The contributor is male, the lesion involves the leg, the photograph is a close-up of the affected area, texture is reported as raised or bumpy and rough or flaky, symptoms reported: itching and burning:
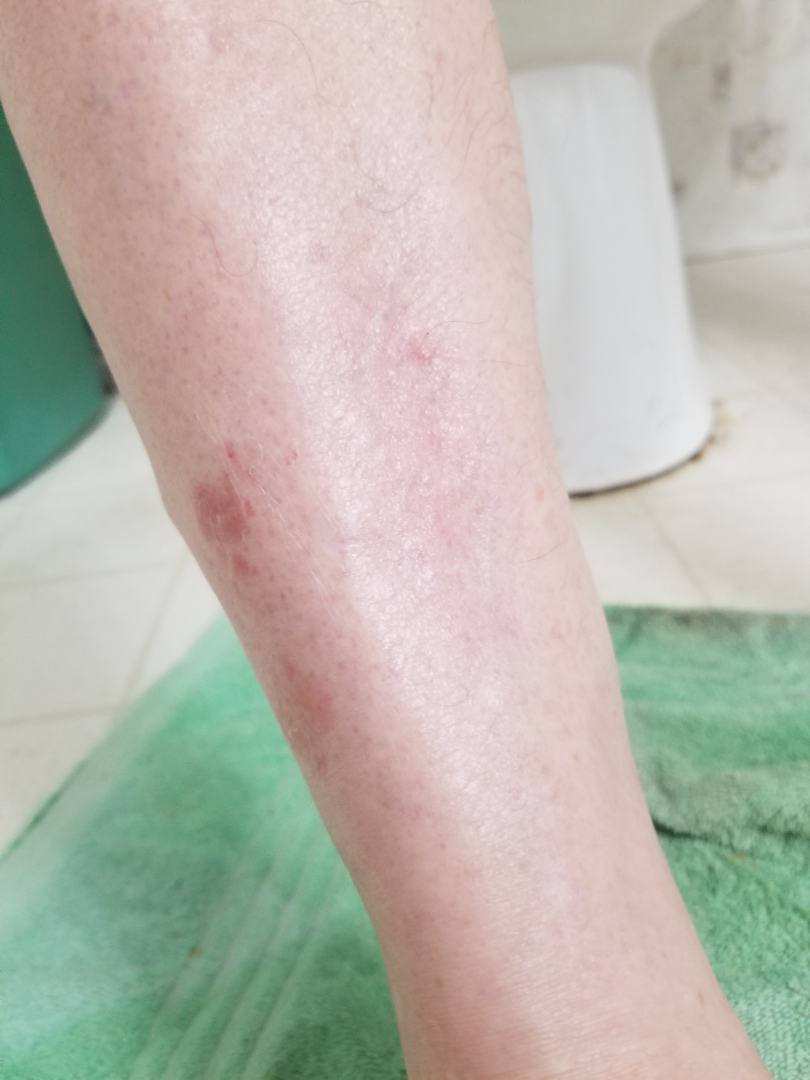Assessment:
No differential diagnosis could be assigned on photographic review.